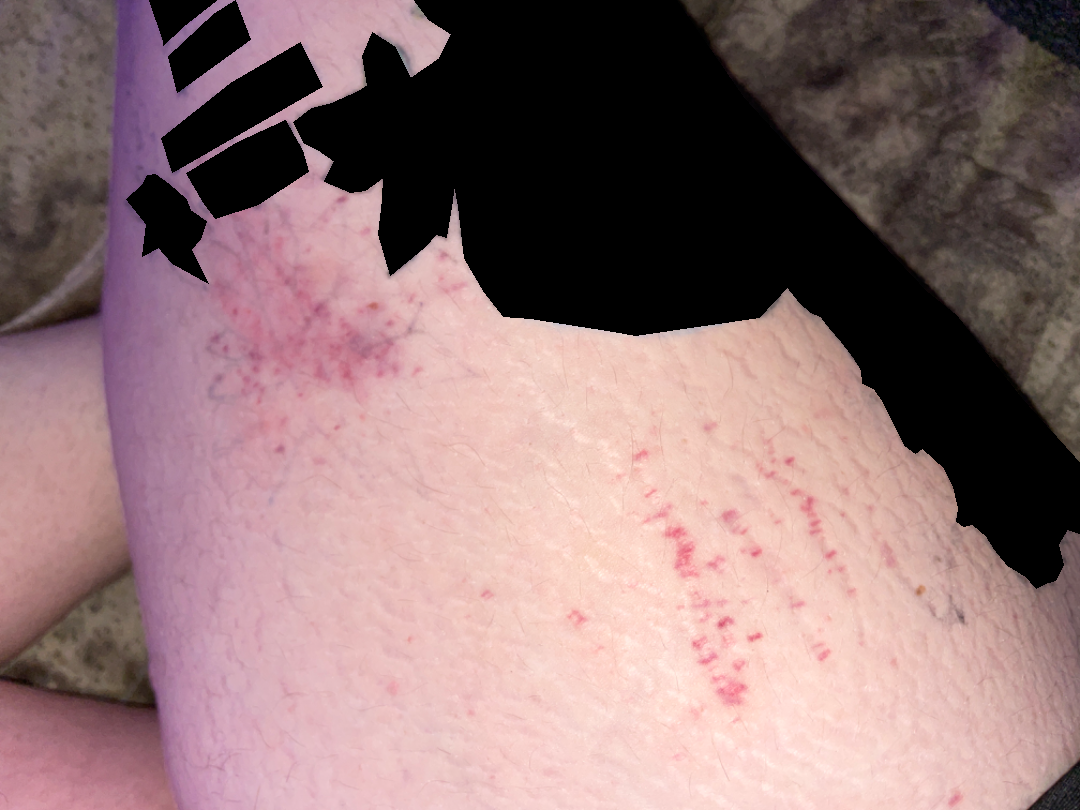The dermatologist could not determine a likely condition from the photograph alone. The patient considered this a rash. The lesion involves the leg. The patient notes the lesion is flat. Female patient, age 18–29. The photo was captured at a distance.